Self-categorized by the patient as a rash · the lesion is described as fluid-filled · this is a close-up image · the contributor is 40–49, female · associated systemic symptoms include chills · the condition has been present for less than one week · the affected area is the leg — 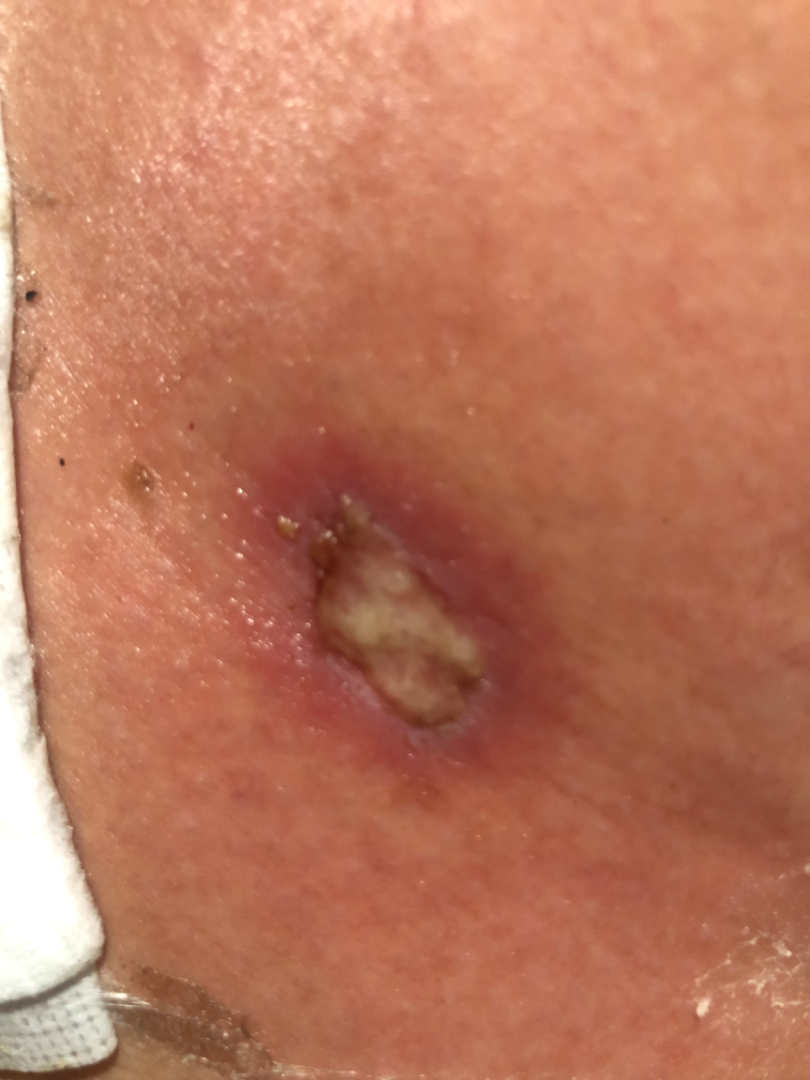Assessment:
The dermatologist could not determine a likely condition from the photograph alone.